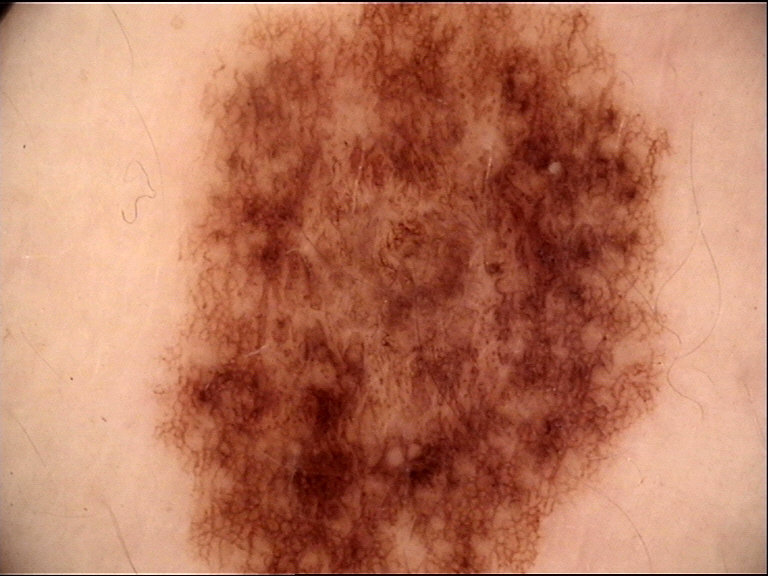imaging — dermoscopy | label — dysplastic compound nevus (expert consensus).